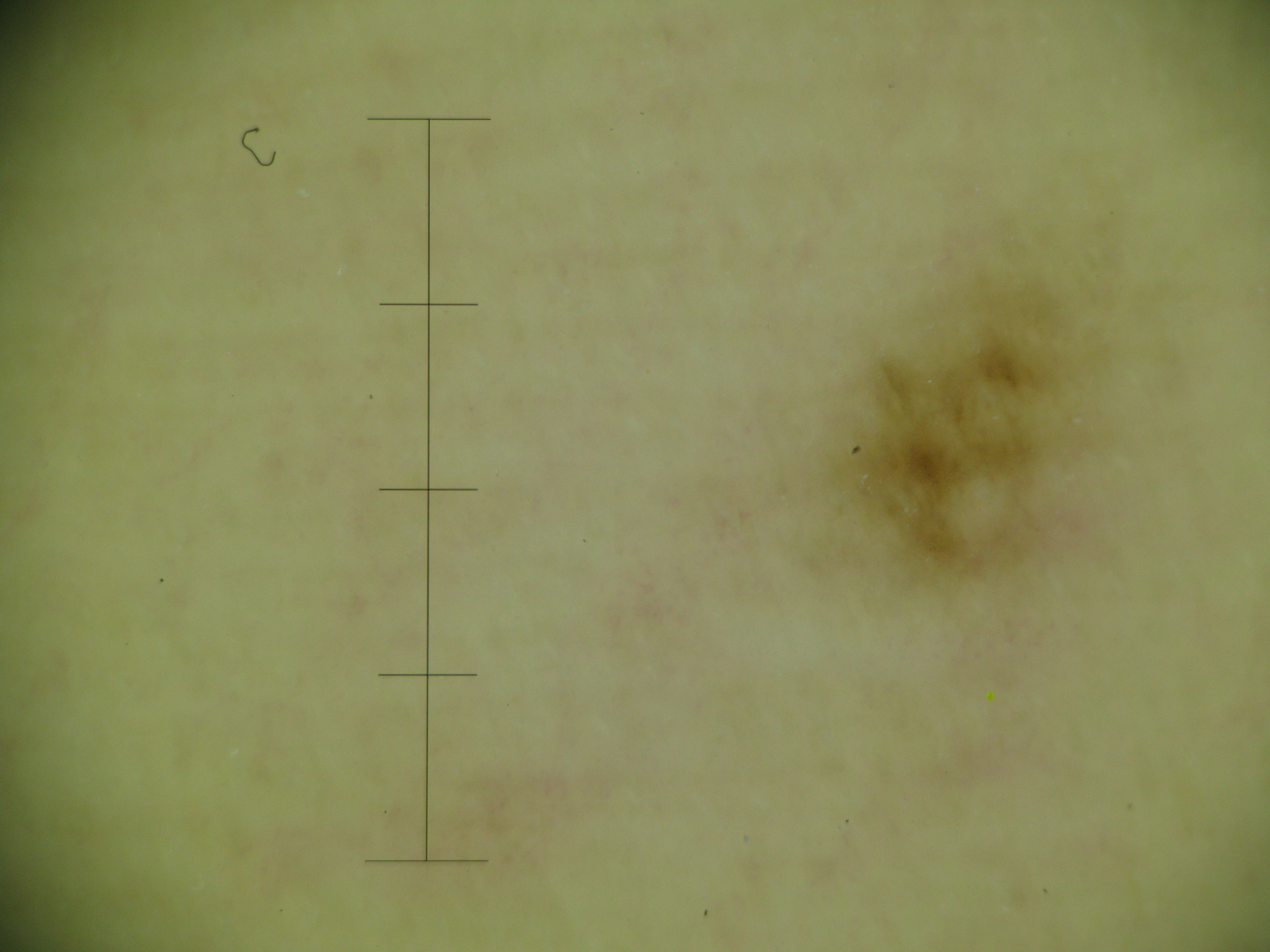Q: What kind of image is this?
A: dermoscopy
Q: What is this lesion?
A: acral junctional nevus (expert consensus)